Recorded as Fitzpatrick phototype IV · a female patient roughly 55 years of age — 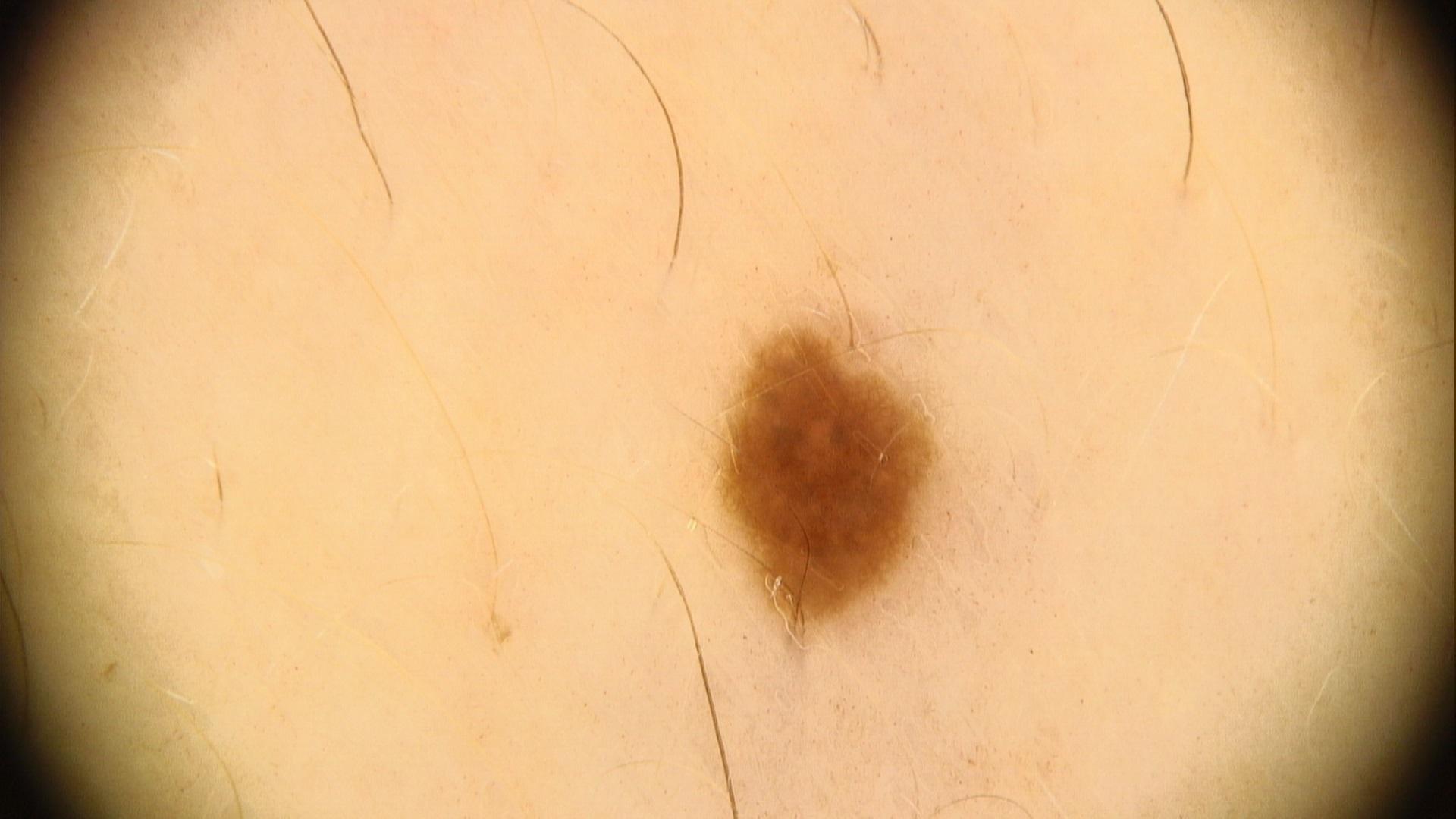* location: a lower extremity
* diagnostic label: Nevus (clinical impression)